A dermoscopic image of a skin lesion:
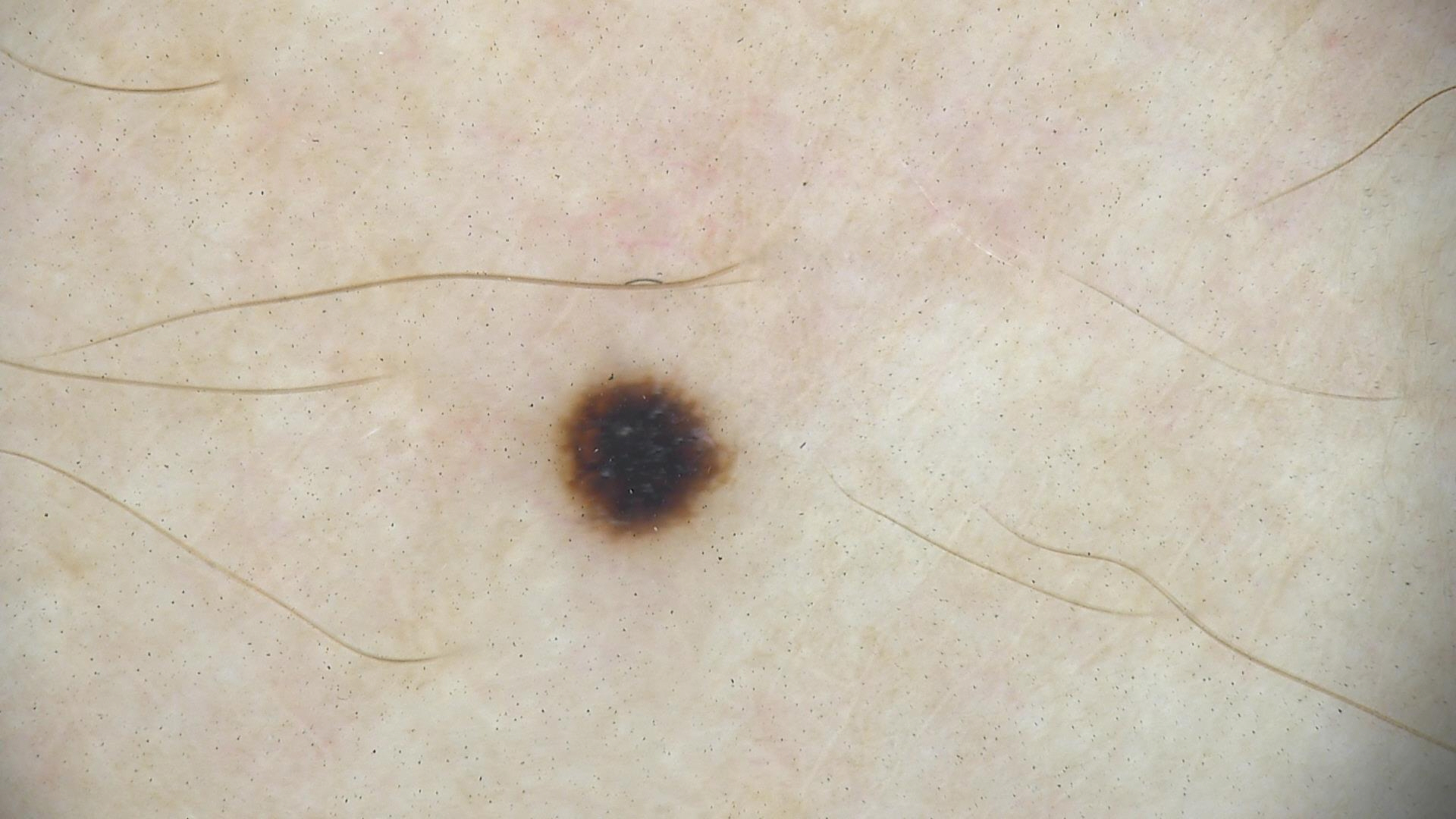| key | value |
|---|---|
| diagnosis | dysplastic junctional nevus (expert consensus) |